This is a close-up image: 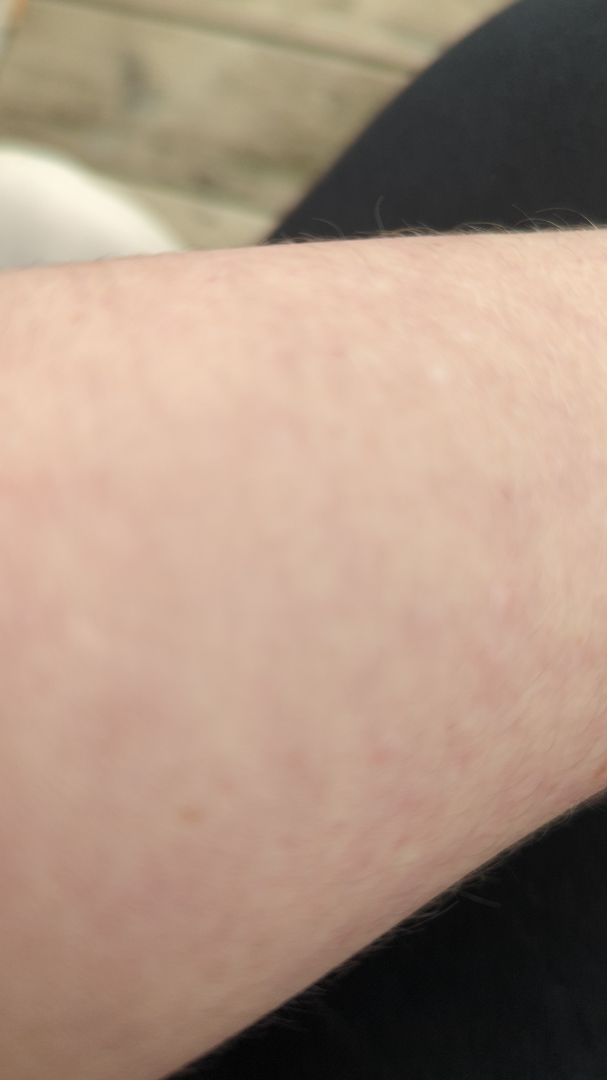The dermatologist could not determine a likely condition from the photograph alone.